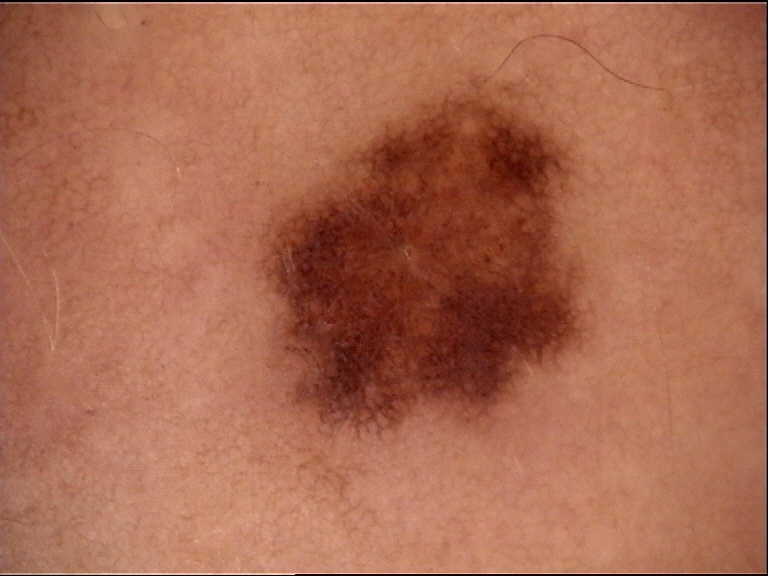<lesion>
<diagnosis>
<name>dysplastic junctional nevus</name>
<code>jd</code>
<malignancy>benign</malignancy>
<super_class>melanocytic</super_class>
<confirmation>expert consensus</confirmation>
</diagnosis>
</lesion>